The lesion involves the leg; no relevant systemic symptoms; the patient reports the condition has been present for three to twelve months; close-up view; the patient described the issue as a rash:
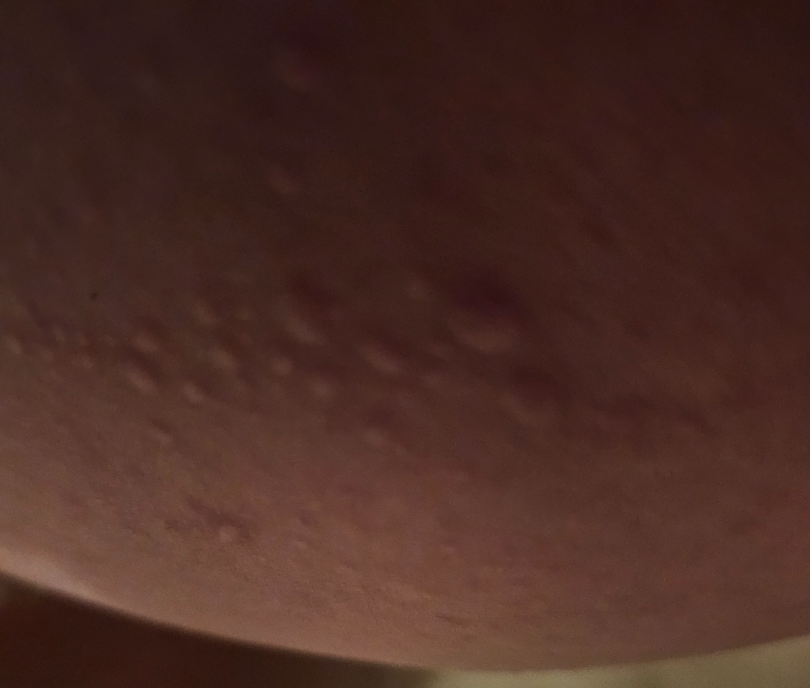Urticaria (most likely).